On a questionnaire the patient reported a personal history of skin cancer, a personal history of cancer, no family history of skin cancer, and no prior organ transplant; a skin lesion imaged with a dermatoscope; a female patient age 60; the patient says their skin tans without first burning; referred with a clinical suspicion of basal cell carcinoma; few moles overall by the patient's own estimate:
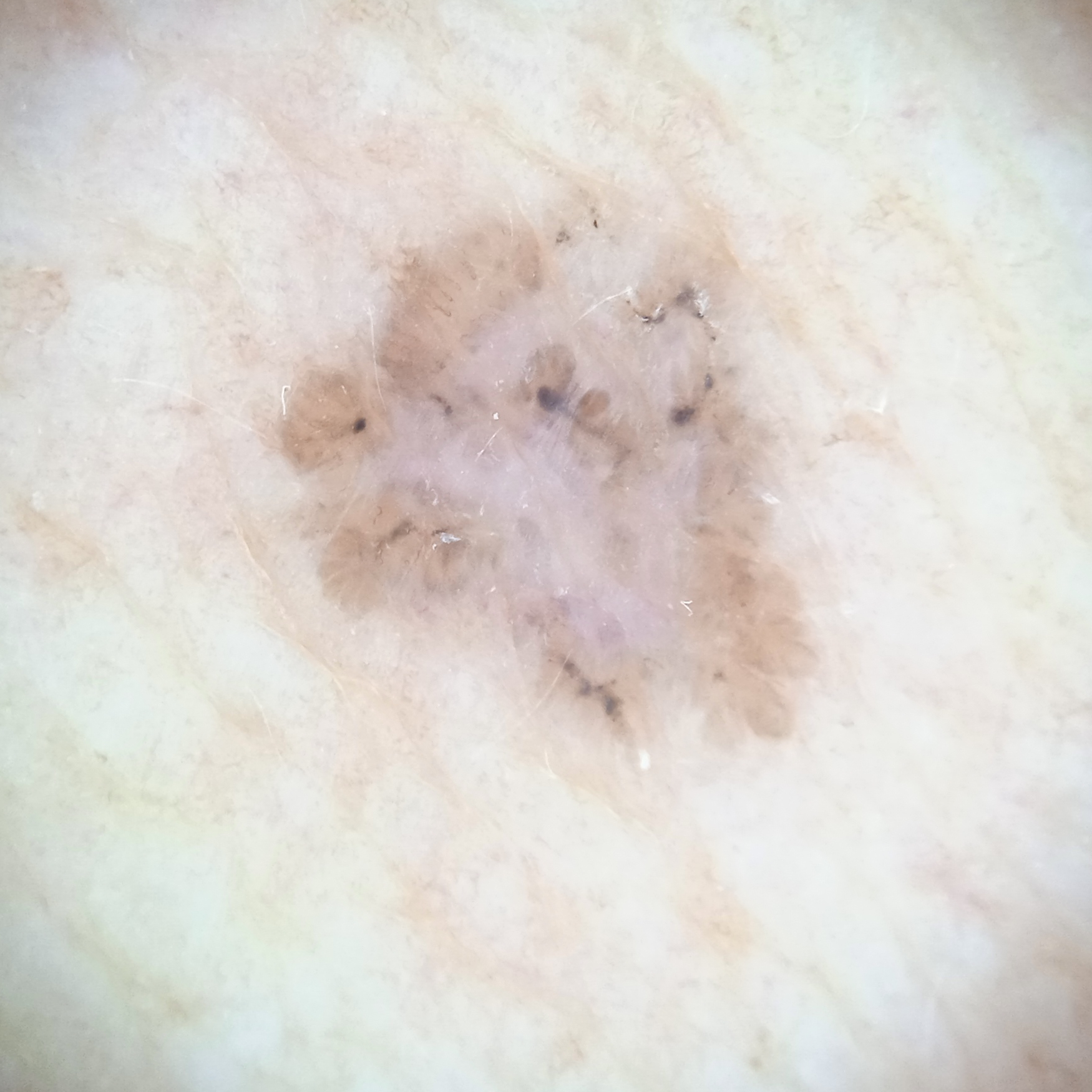Findings: Located on the torso. The lesion is about 7.2 mm across. Conclusion: The dermatologists' assessment was a basal cell carcinoma.